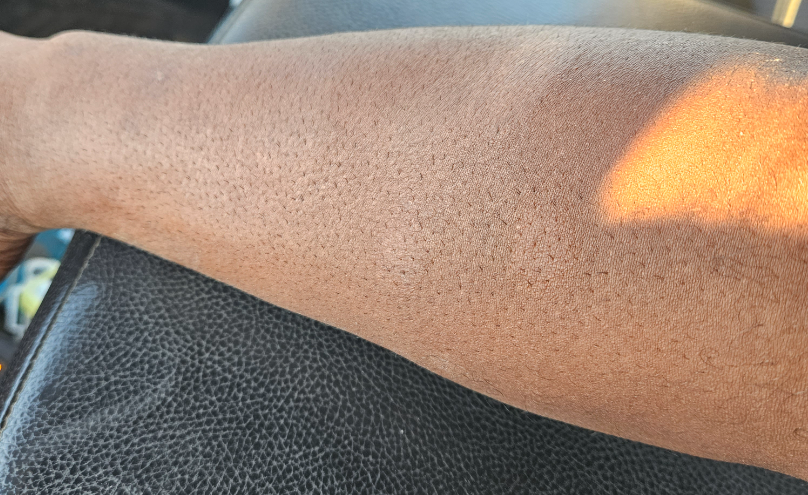The case was indeterminate on photographic review. The photo was captured at a distance. The contributor is a male aged 40–49. The affected area is the arm and head or neck. Skin tone: Fitzpatrick phototype V. Reported lesion symptoms include itching. Texture is reported as raised or bumpy.